Dermoscopy of a skin lesion:
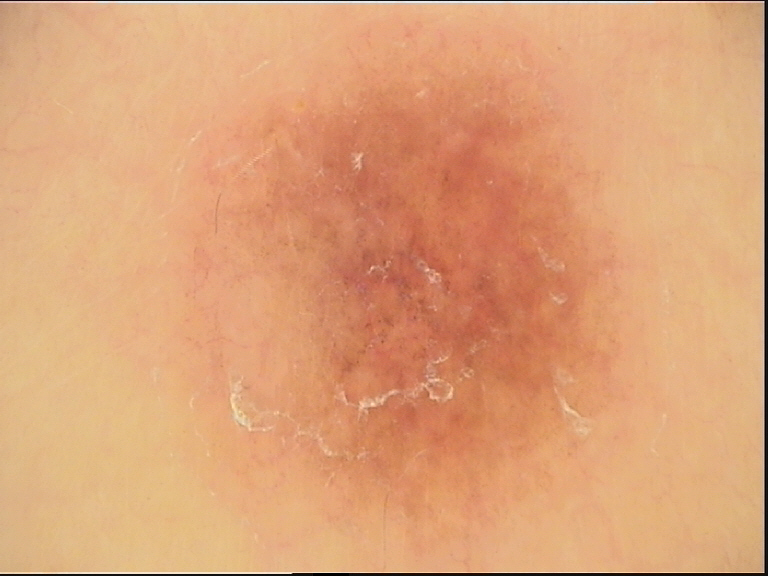{"diagnosis": {"name": "dysplastic junctional nevus", "code": "jd", "malignancy": "benign", "super_class": "melanocytic", "confirmation": "expert consensus"}}